This image was taken at an angle · skin tone: Fitzpatrick phototype IV.
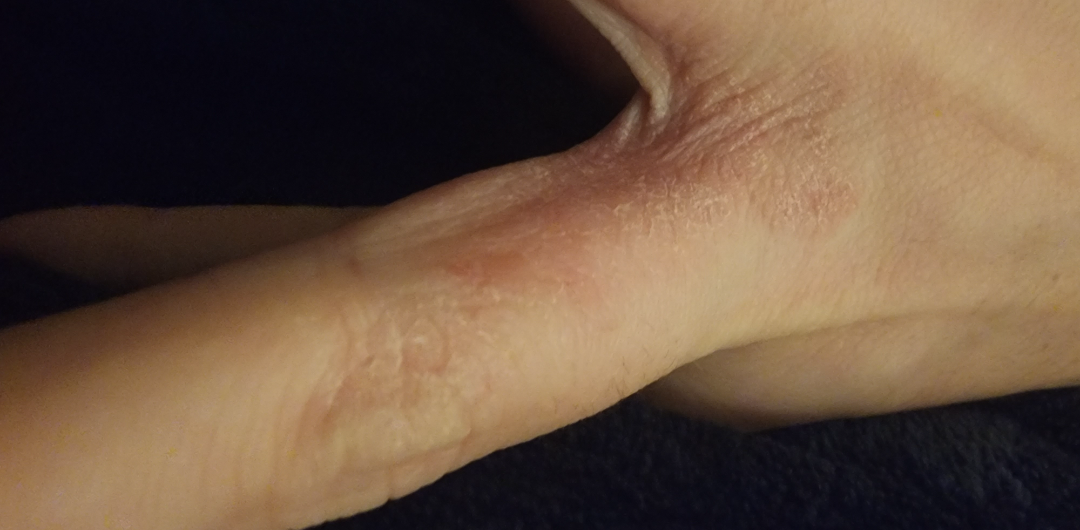{"differential": {"leading": ["Eczema"], "considered": ["Tinea", "Psoriasis"]}}